The photo was captured at a distance · the affected area is the arm:
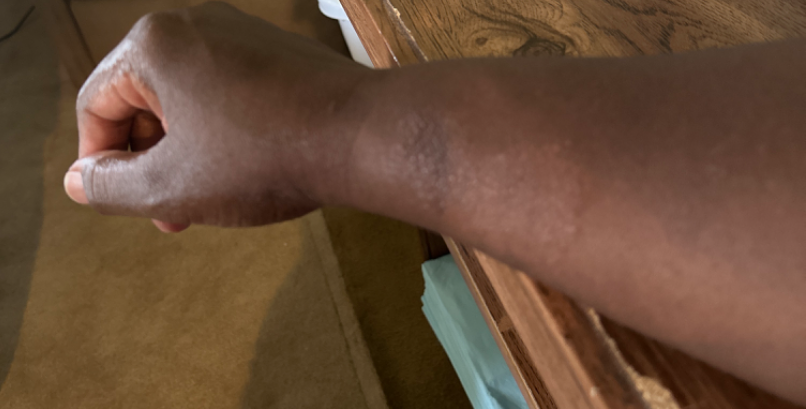The skin condition could not be confidently assessed from this image.